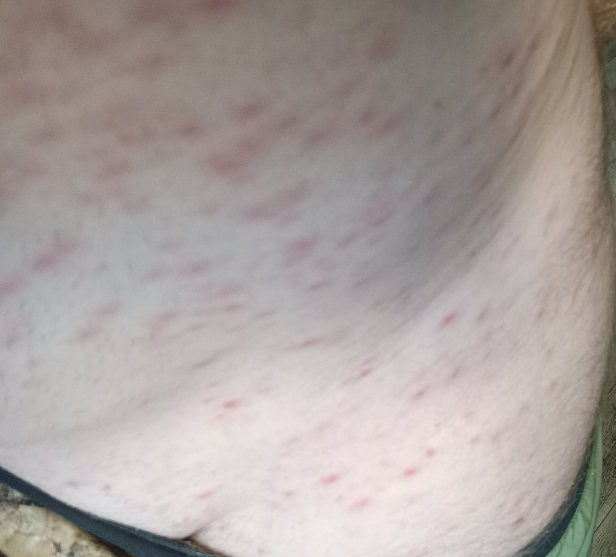view=at an angle.